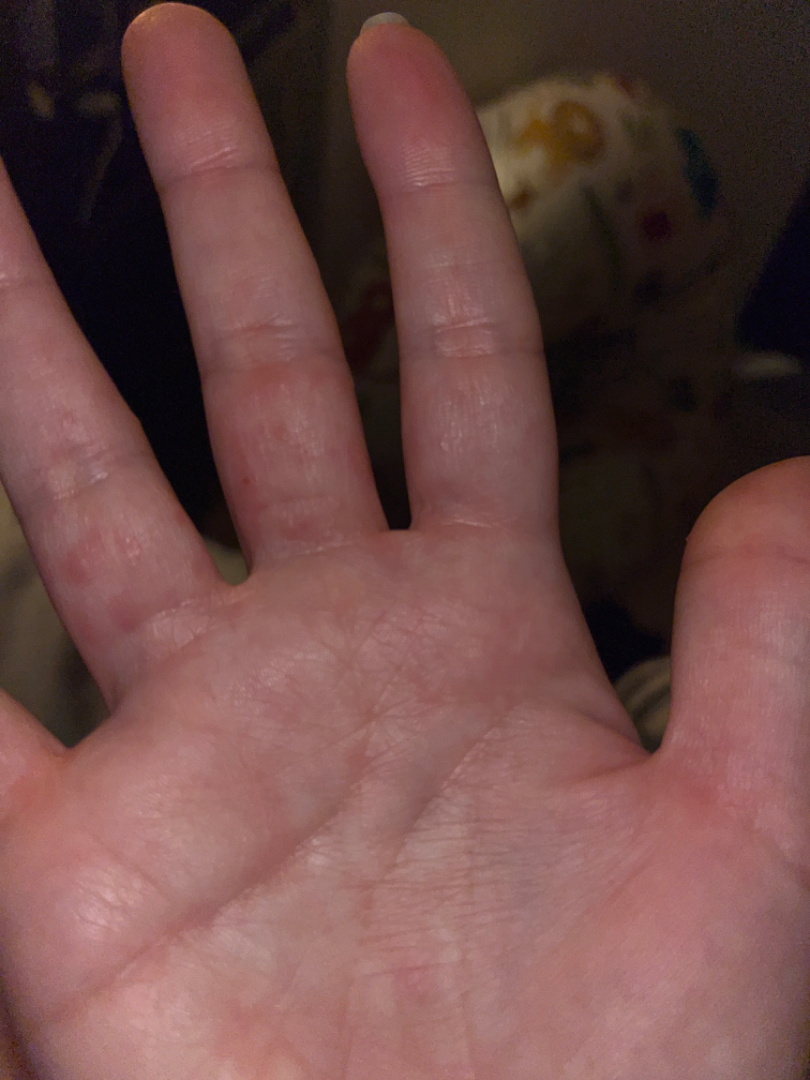The reviewing panel's impression was: Scabies (most likely); Eczema (considered).